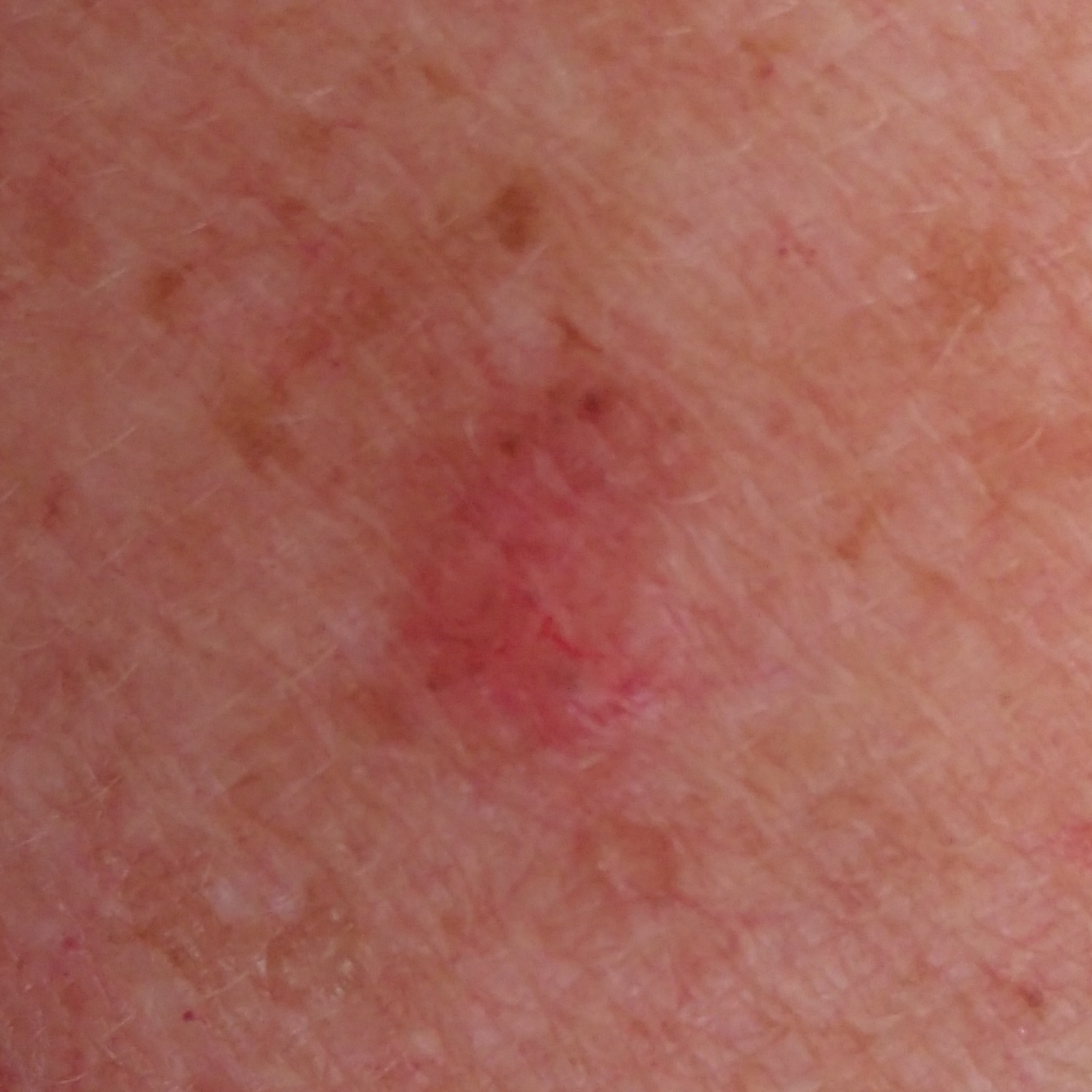A clinical photograph showing a skin lesion. A female patient in their late 40s. The lesion was found on the chest. Per patient report, the lesion itches and is elevated, but does not hurt. Confirmed on histopathology as a basal cell carcinoma.